A dermoscopic close-up of a skin lesion.
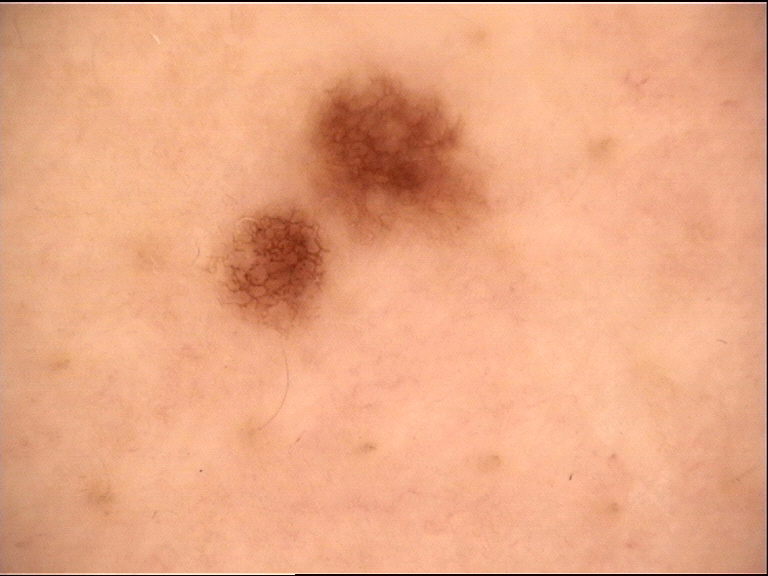assessment — dysplastic junctional nevus (expert consensus)